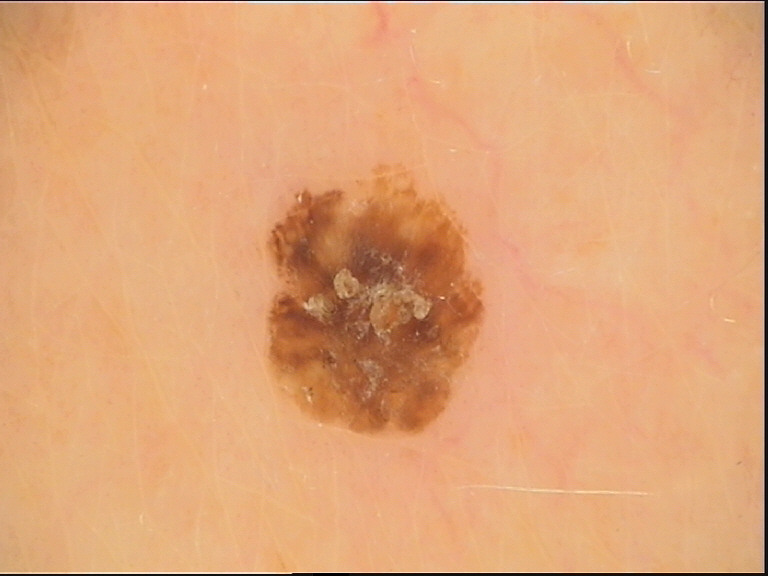label — seborrheic keratosis (expert consensus).